The photograph was taken at an angle · the patient described the issue as skin that appeared healthy to them · the contributor reports the condition has been present for less than one week · texture is reported as rough or flaky and raised or bumpy · located on the front of the torso, back of the torso and head or neck.
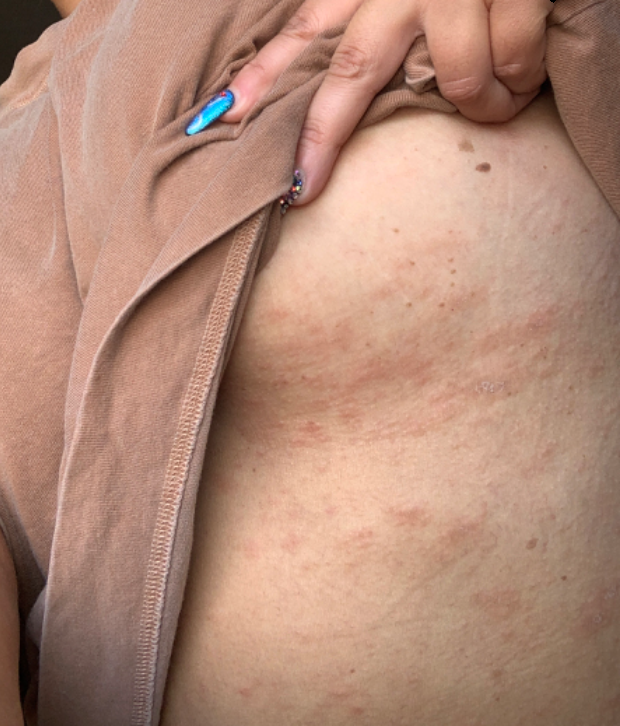Notes:
- assessment: ungradable on photographic review